A dermatoscopic image of a skin lesion:
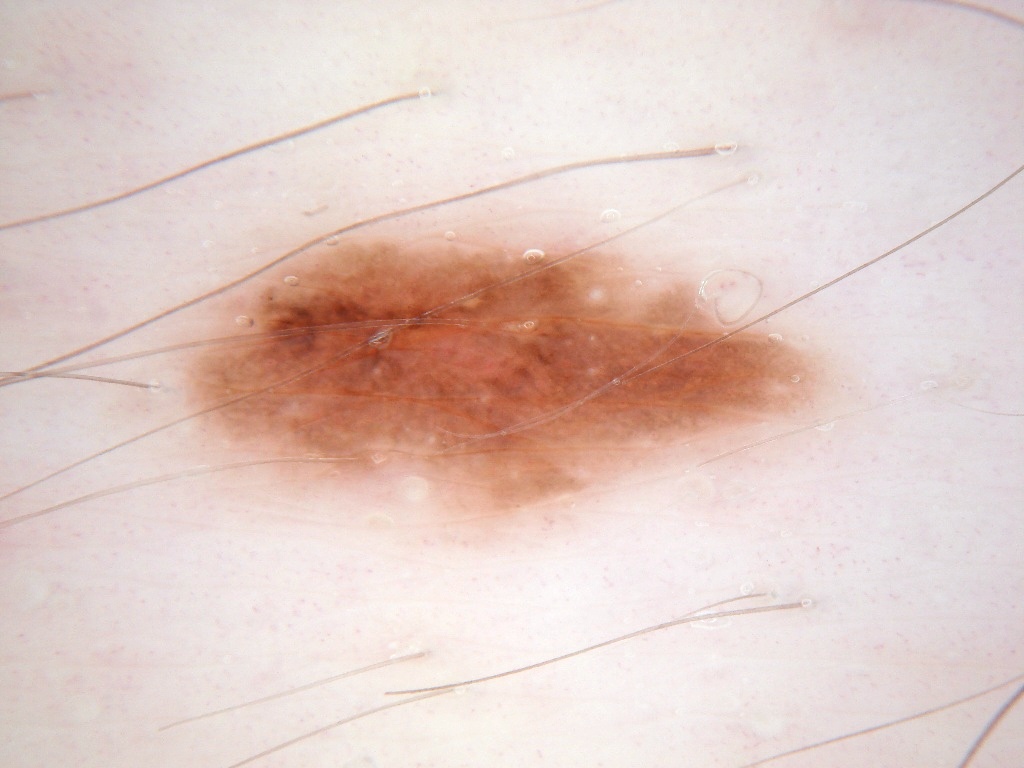{"dermoscopic_features": {"present": ["pigment network", "milia-like cysts"], "absent": ["streaks", "negative network", "globules"]}, "lesion_location": {"bbox_xyxy": [165, 218, 848, 555]}, "diagnosis": {"name": "melanocytic nevus", "malignancy": "benign", "lineage": "melanocytic", "provenance": "clinical"}}